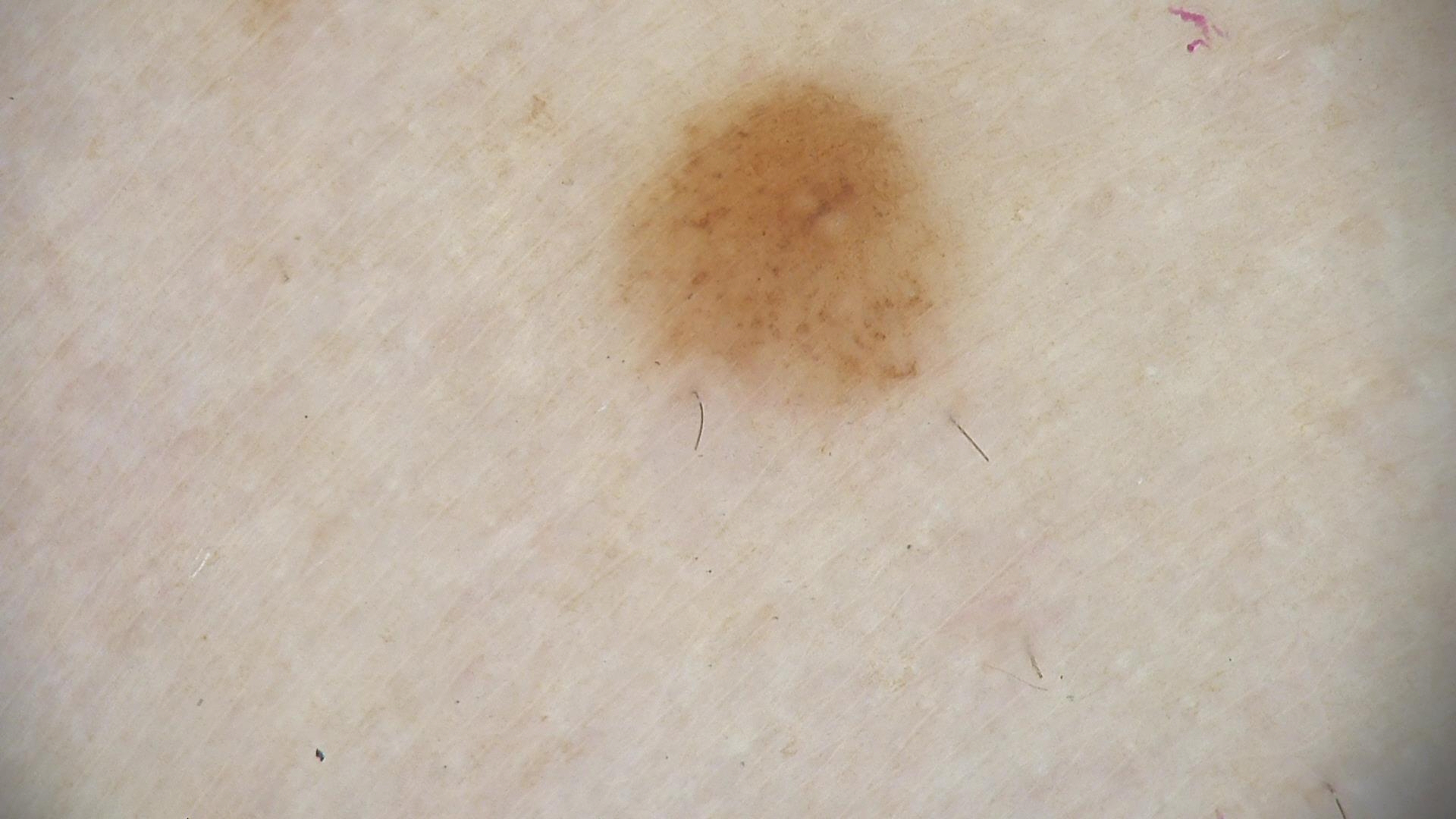A dermoscopic photograph of a skin lesion. Consistent with a benign lesion — a dysplastic junctional nevus.